A clinical photo of a skin lesion taken with a smartphone; a male subject 71 years of age: 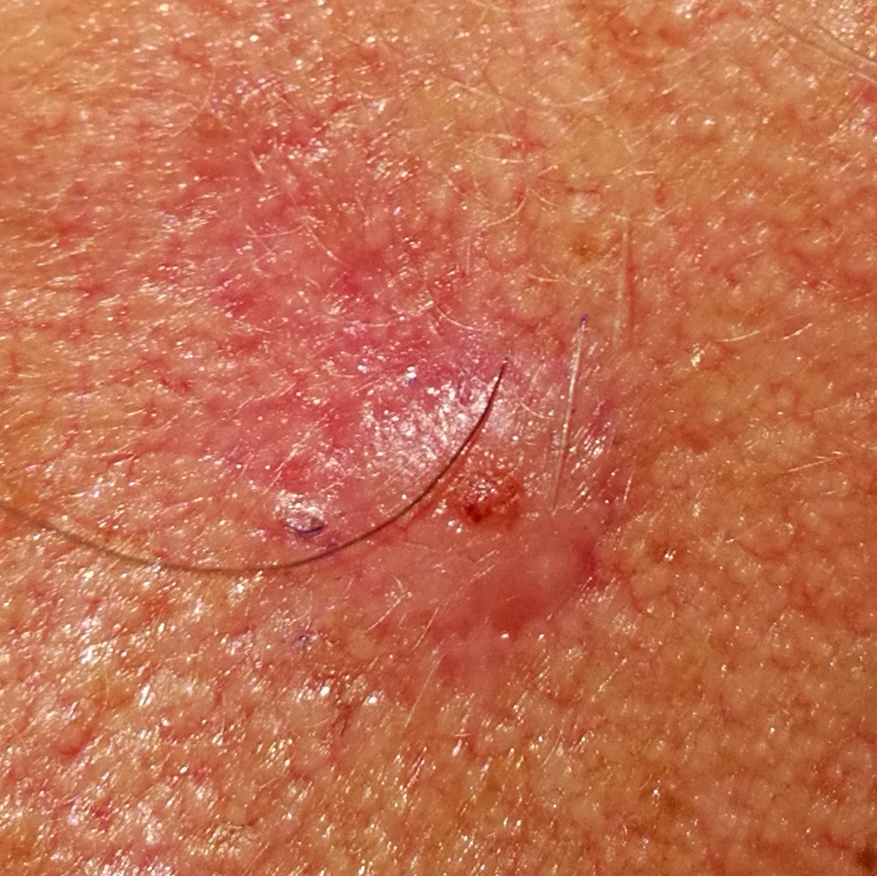Q: Where on the body is the lesion?
A: the face
Q: What does the patient describe?
A: bleeding, itching, elevation, pain
Q: What is the diagnosis?
A: basal cell carcinoma (biopsy-proven)